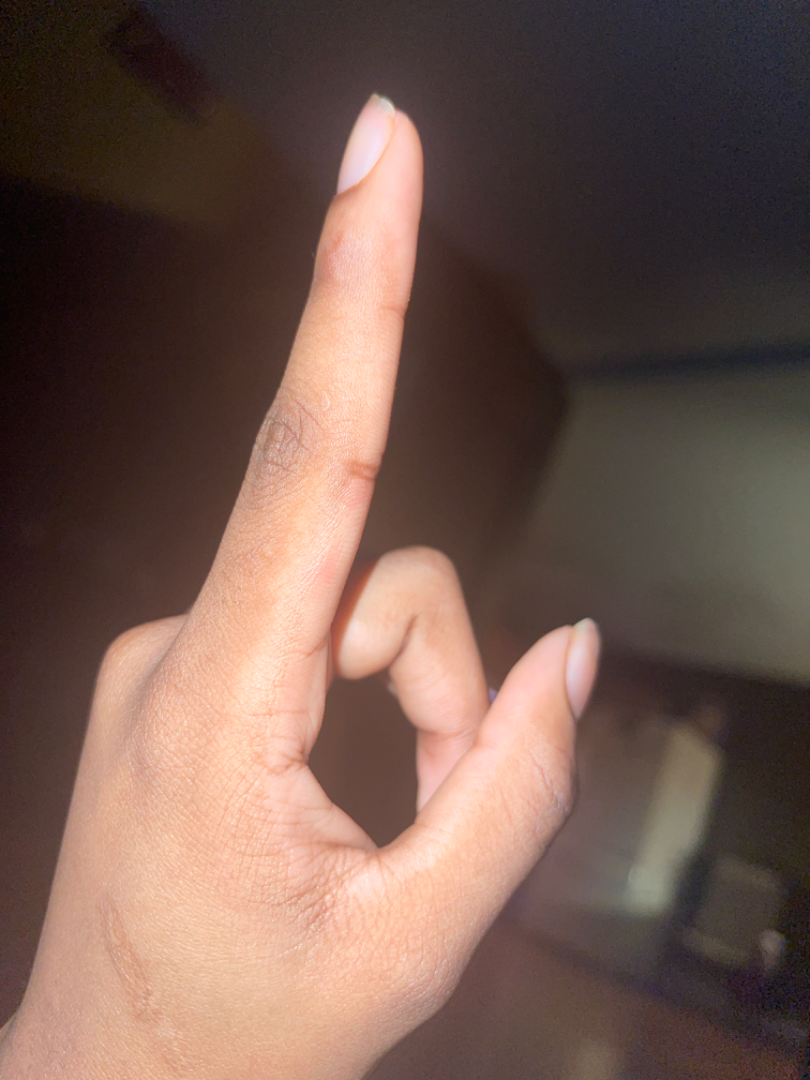Notes:
* onset: about one day
* reported symptoms: burning, itching and bothersome appearance
* associated systemic symptoms: none reported
* patient describes the issue as: acne
* patient: female, age 18–29
* site: top or side of the foot, back of the hand and sole of the foot
* framing: at a distance
* texture: fluid-filled and raised or bumpy